A dermoscopic photograph of a skin lesion.
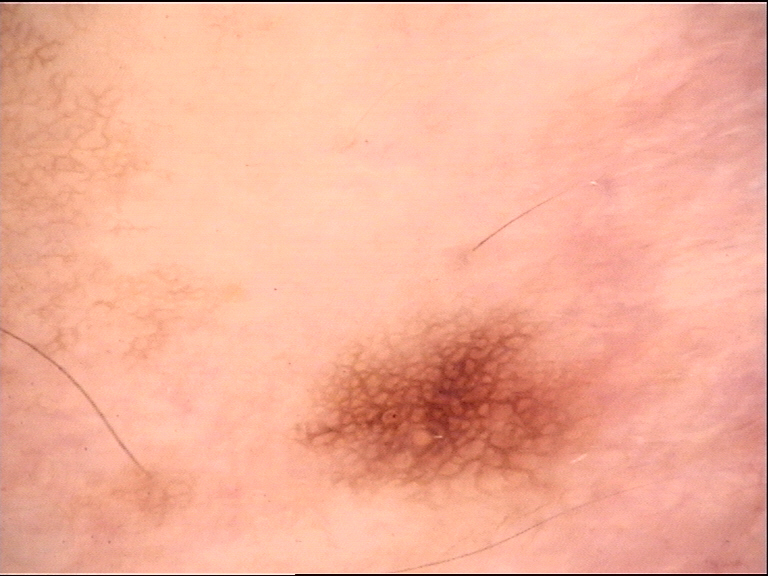Conclusion: Diagnosed as a dysplastic junctional nevus.